The patient is a female in their mid-30s; a dermoscopic image of a skin lesion — 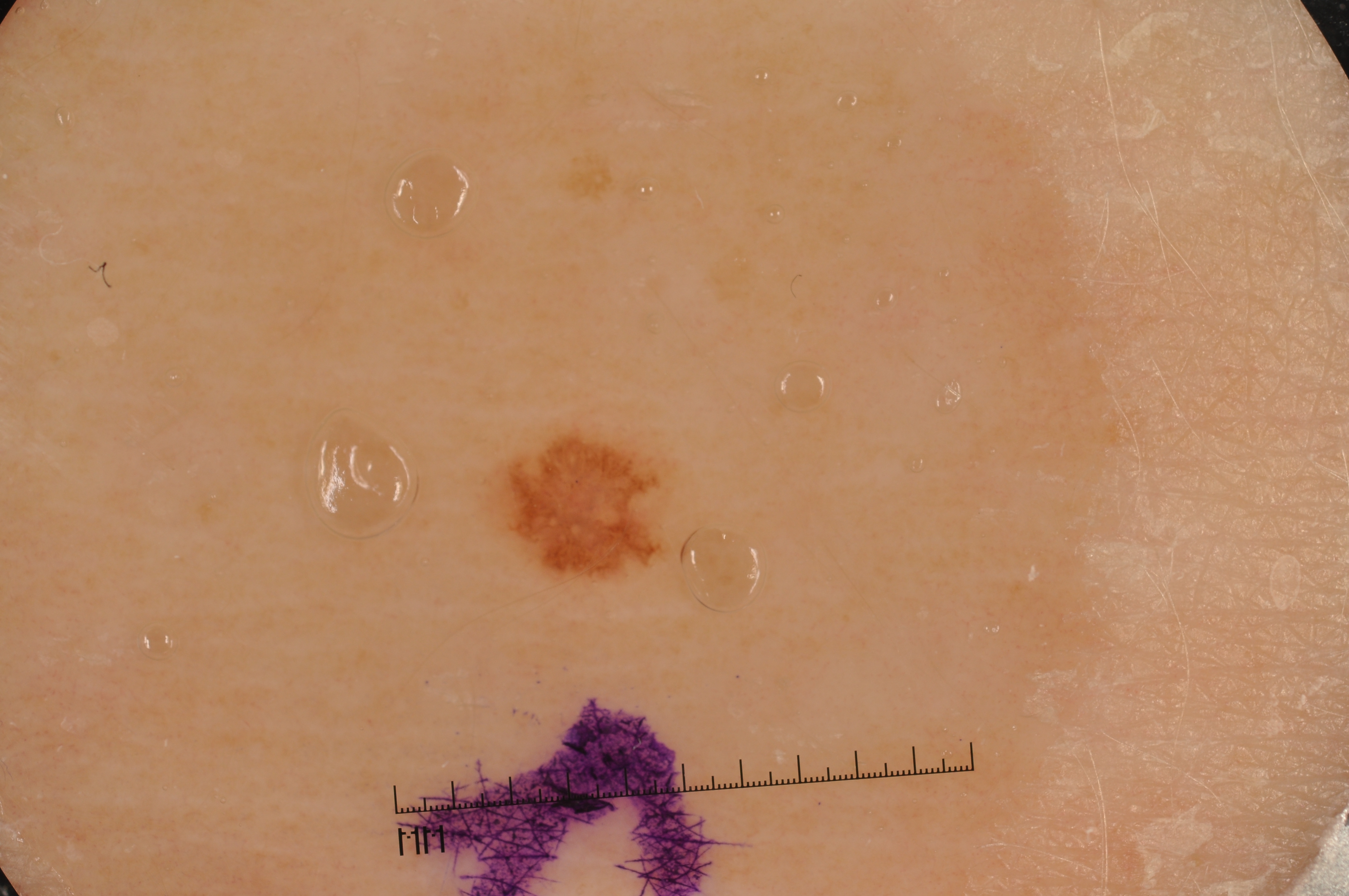Case summary: Dermoscopic review identifies pigment network. In (x1, y1, x2, y2) order, the lesion's extent is (495, 434, 664, 574). A small lesion within a wider field of skin. Assessment: The clinical diagnosis was a melanocytic nevus.